Skin tone: lay reviewers estimated Monk Skin Tone 3 (US pool) or 2 (India pool); close-up view.
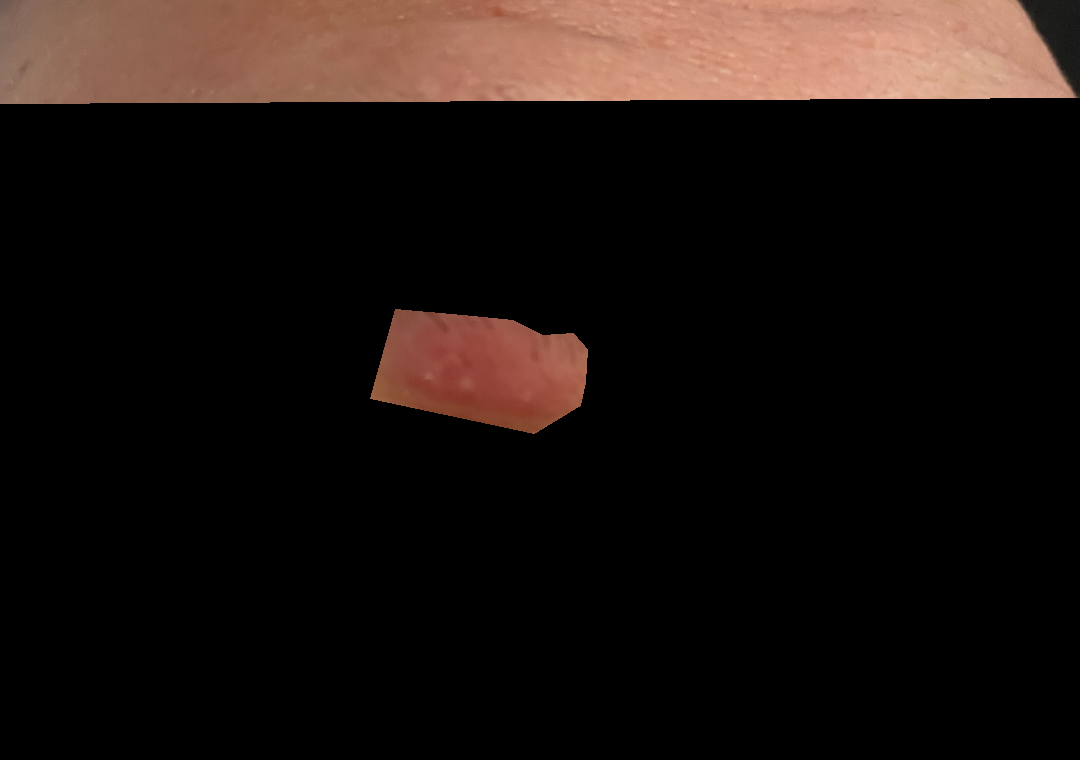Impression: The case was difficult to assess from the available photograph.